The arm is involved; female subject, age 30–39; the photo was captured at an angle.
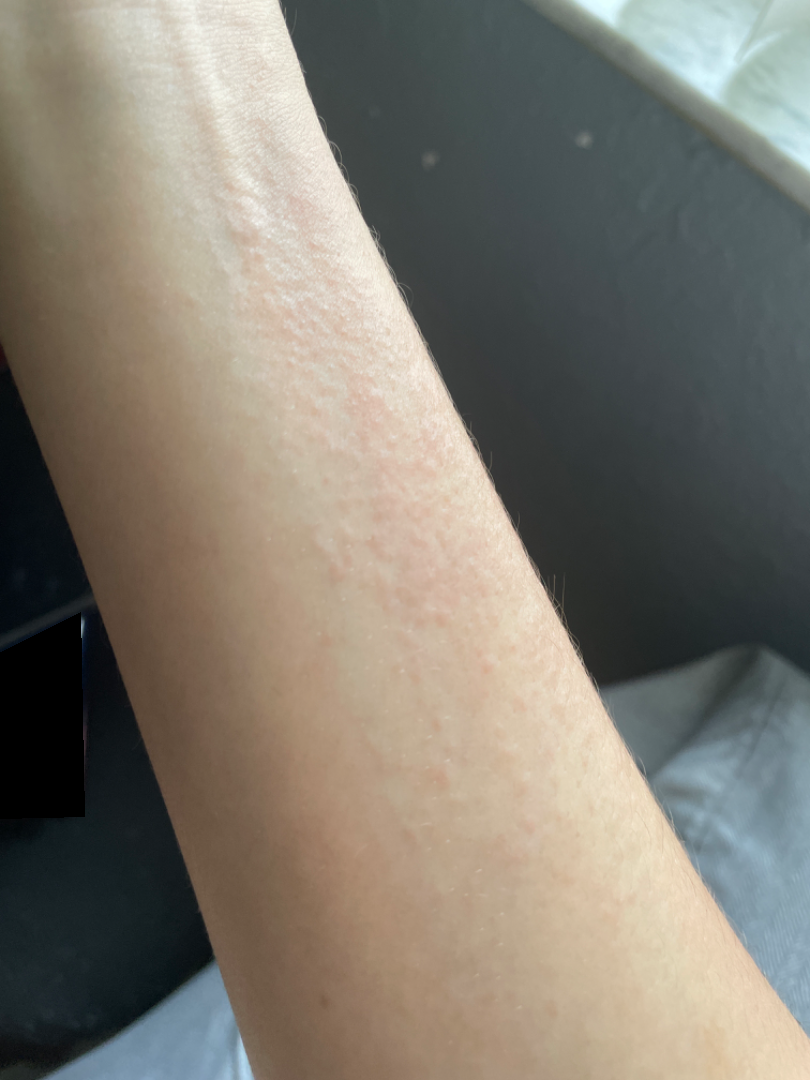Q: Fitzpatrick or Monk tone?
A: lay reviewers estimated MST 3–4
Q: Reported symptoms?
A: itching
Q: Texture?
A: raised or bumpy
Q: How long has this been present?
A: about one day
Q: What is the dermatologist's impression?
A: in keeping with Eczema